A dermatoscopic image of a skin lesion: 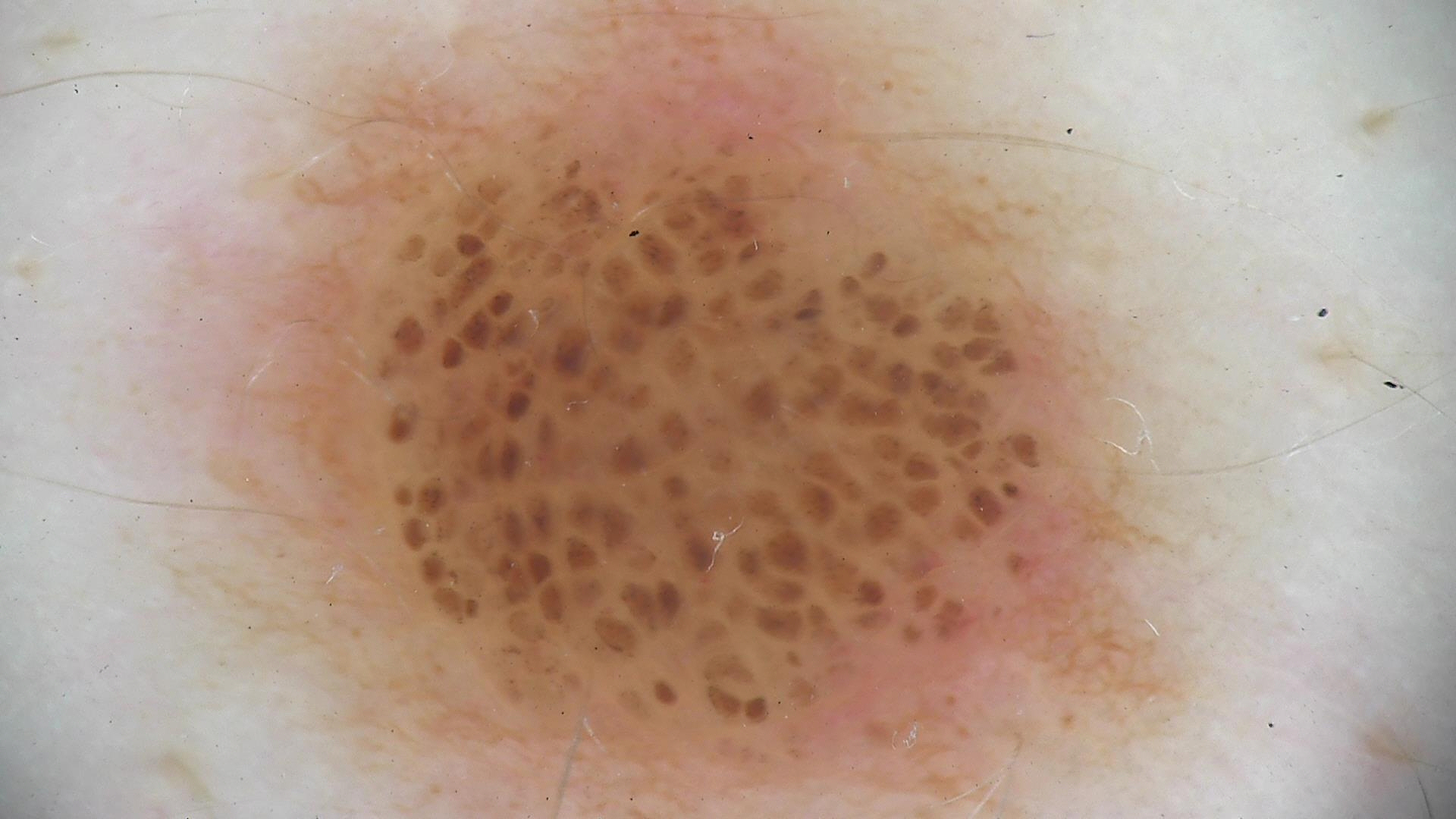class=compound nevus (expert consensus).